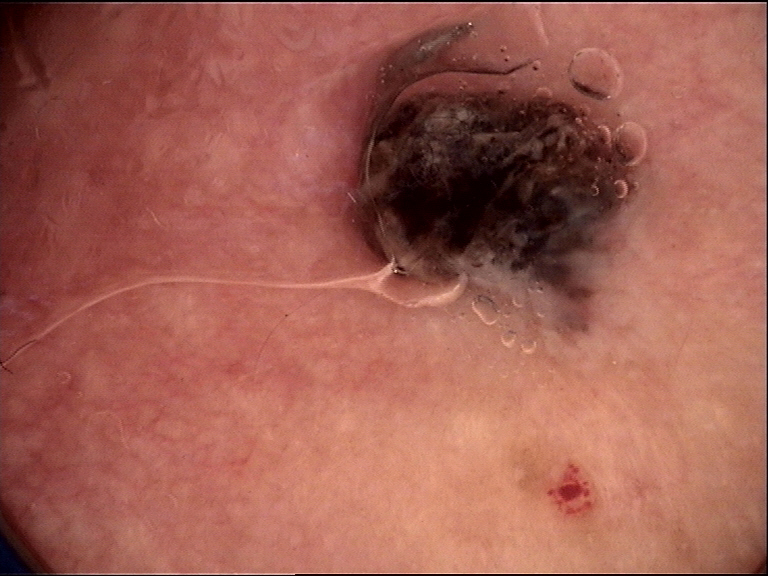diagnosis: melanoma (biopsy-proven).